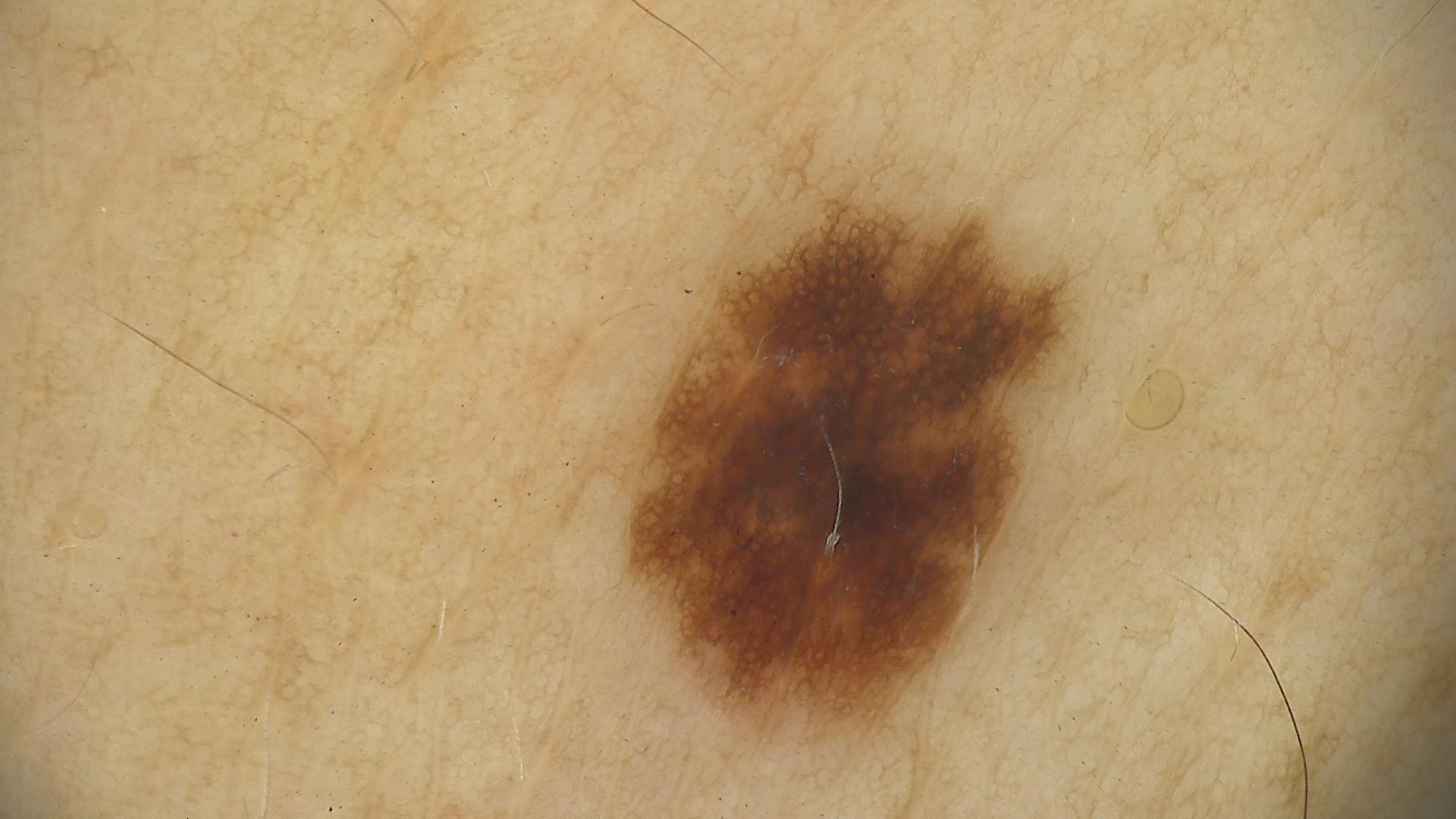image type = dermoscopy; assessment = dysplastic junctional nevus (expert consensus).